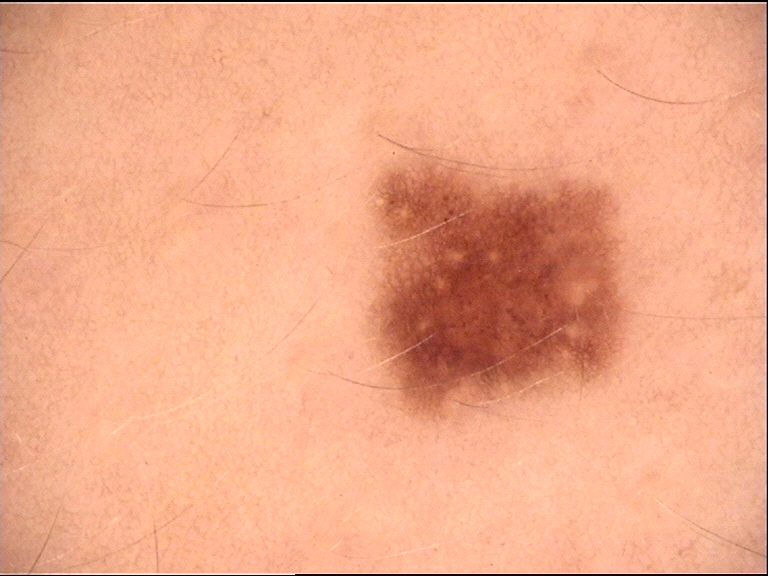Summary: A skin lesion imaged with a dermatoscope. Conclusion: Classified as a dysplastic junctional nevus.